A female patient 64 years of age. Referred for assessment of suspected basal cell carcinoma. A dermoscopy image of a skin lesion:
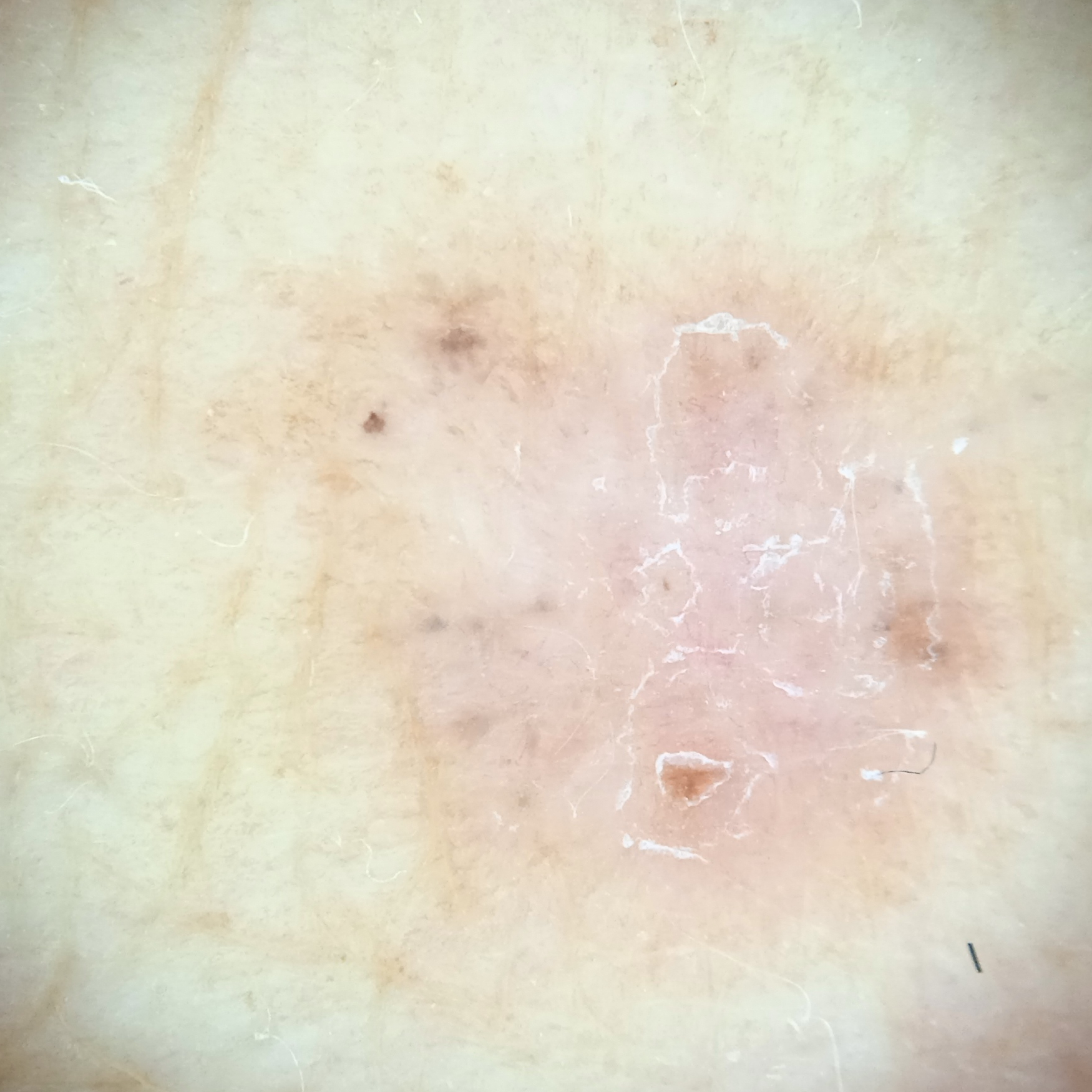Case summary:
The lesion is on the torso. Measuring roughly 8.1 mm.
Diagnosis:
Histopathologically confirmed as a basal cell carcinoma, following a punch biopsy, with a measured thickness of 0.6 mm.